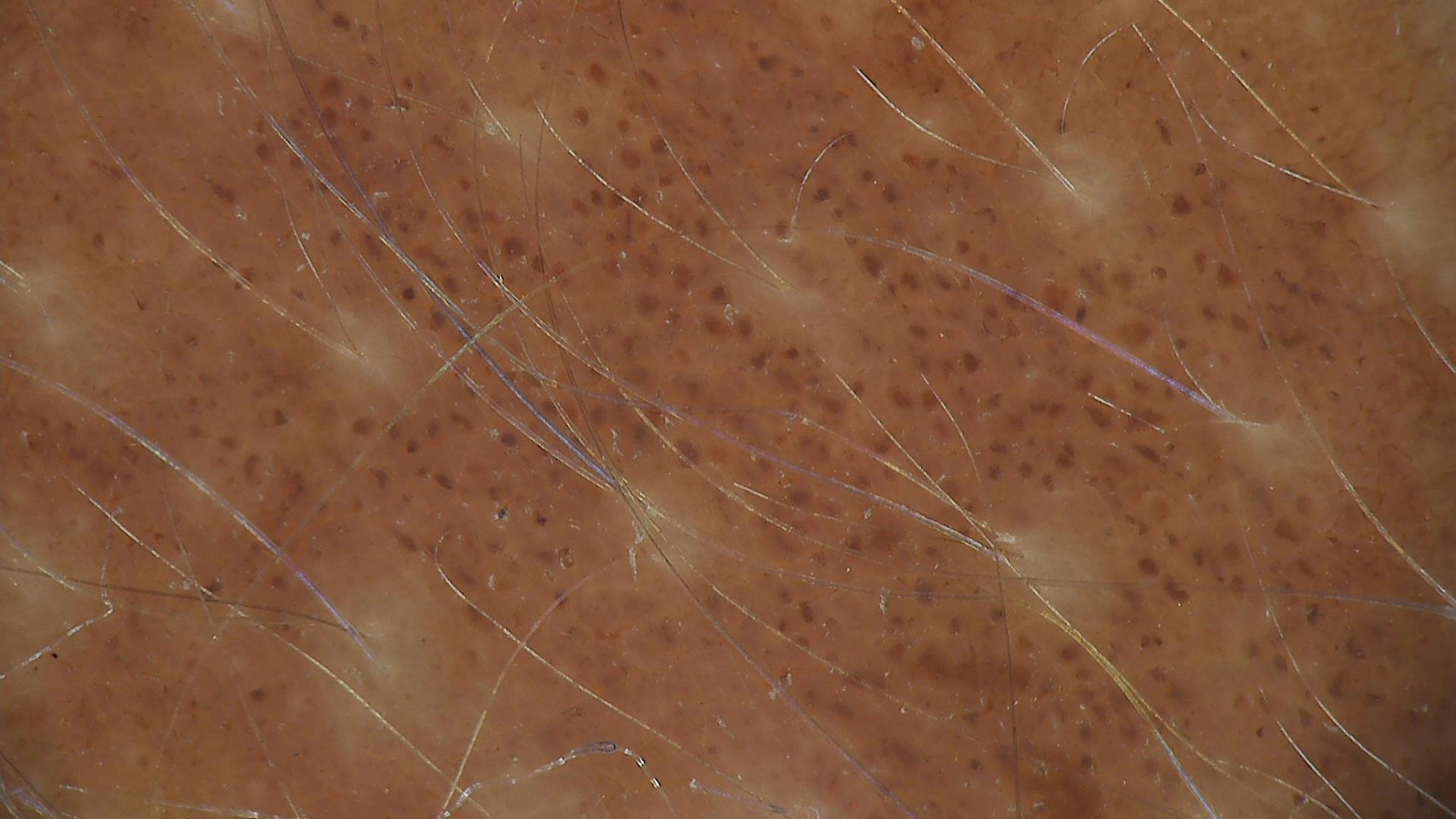Q: What kind of image is this?
A: dermatoscopy
Q: How is the lesion classified?
A: banal
Q: What was the diagnostic impression?
A: congenital junctional nevus (expert consensus)